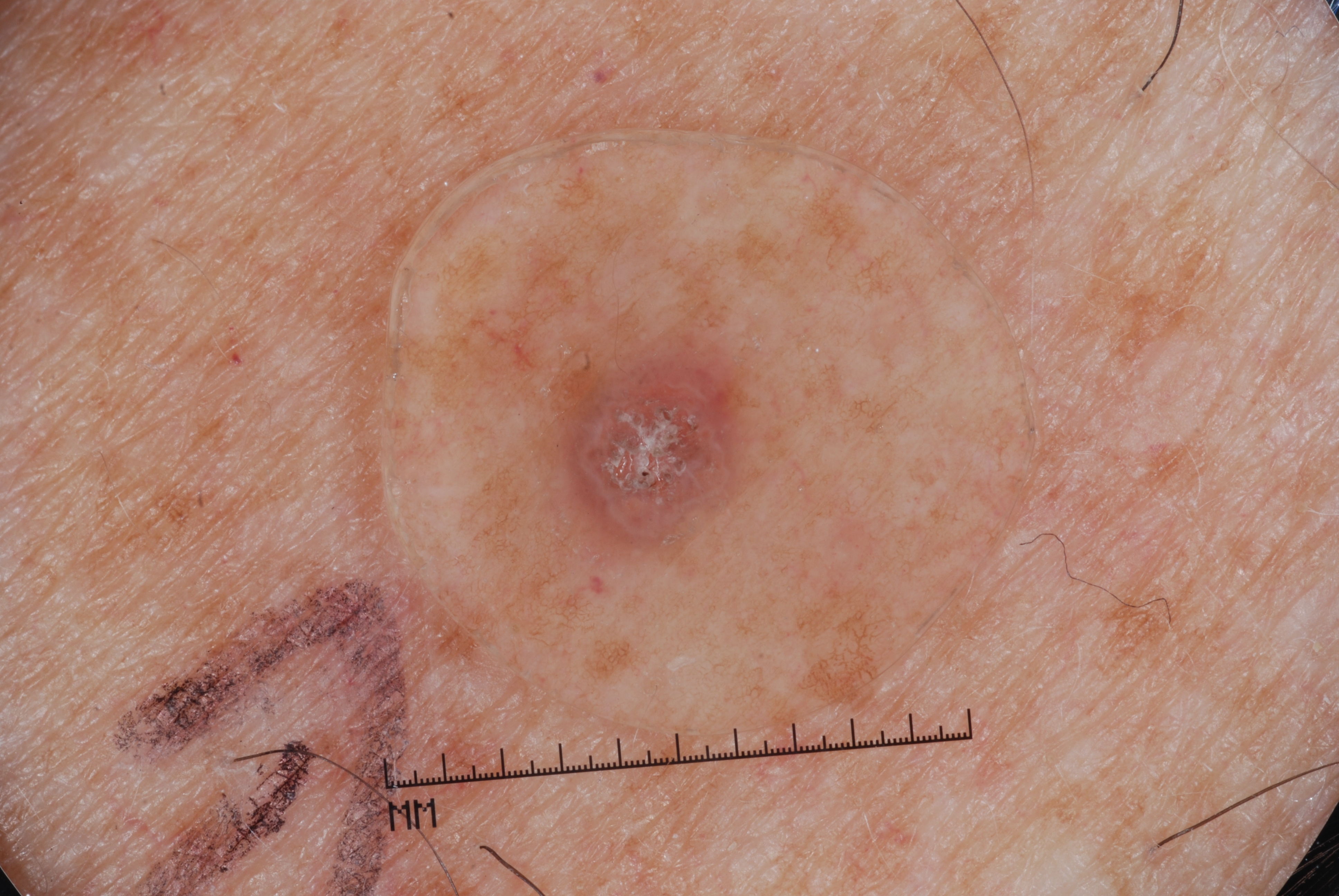Case summary:
* subject: male, in their mid- to late 70s
* imaging: dermatoscopic image of a skin lesion
* lesion bbox: 531 302 761 566
* absent dermoscopic features: milia-like cysts, pigment network, negative network, and streaks
* diagnostic label: a seborrheic keratosis, a benign skin lesion